Texture is reported as raised or bumpy, the photograph is a close-up of the affected area, the lesion involves the leg and top or side of the foot, skin tone: Fitzpatrick skin type III; lay graders estimated Monk Skin Tone 5 (US pool) or 2 (India pool): 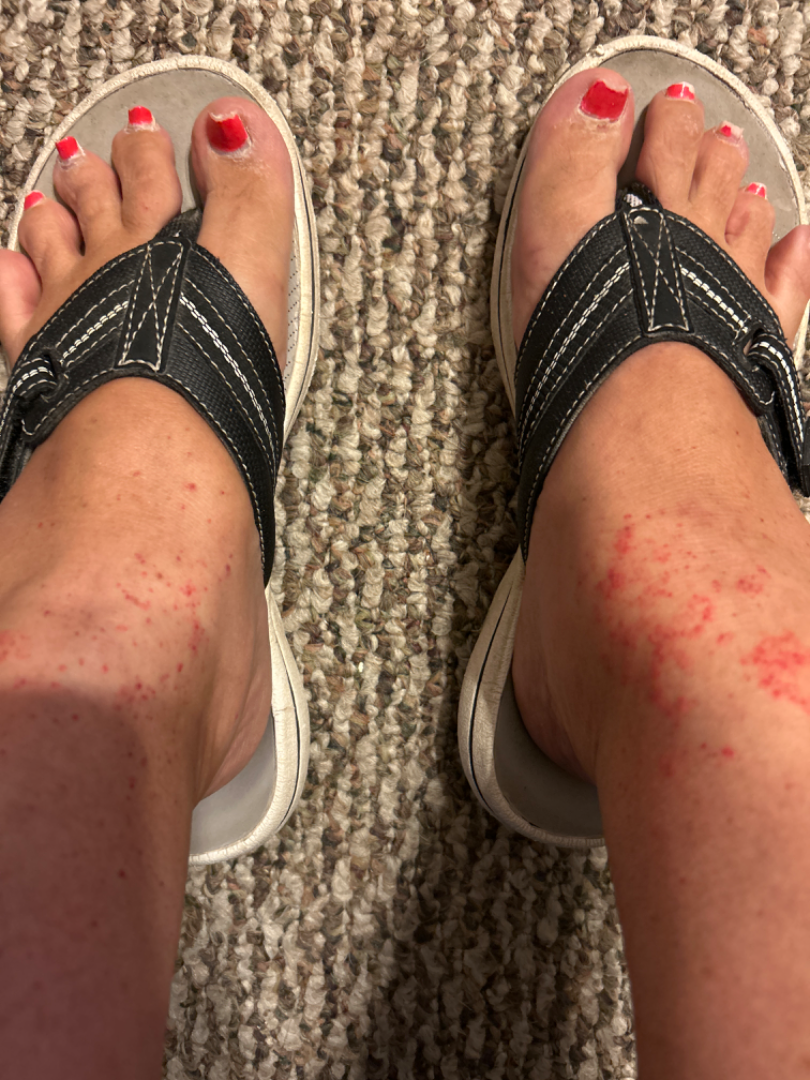On photographic review, the primary impression is Pigmented purpuric eruption; also on the differential is Purpura; an alternative is Vasculitis of the skin.